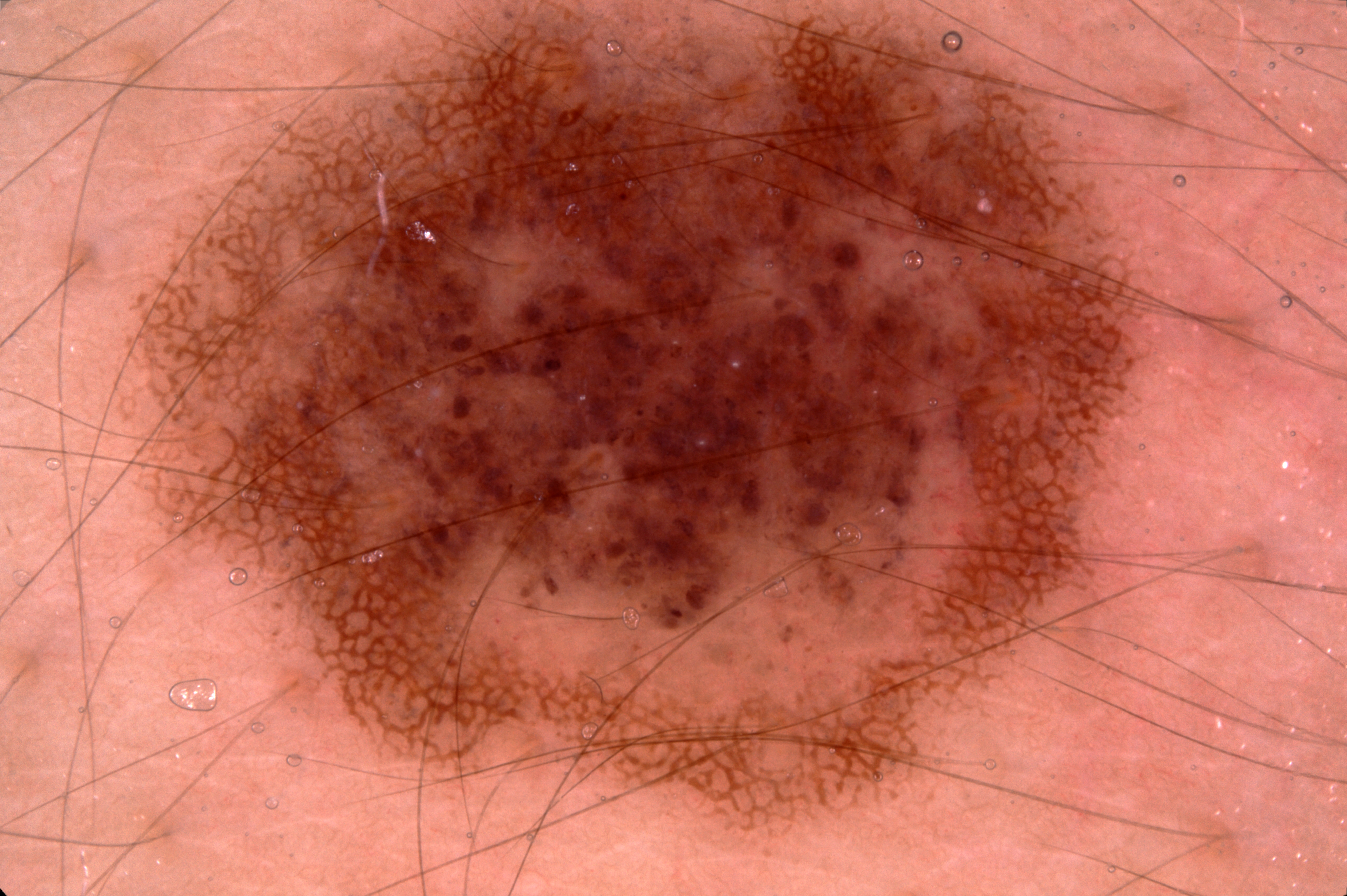image type = dermoscopy of a skin lesion | features = pigment network; absent: negative network, streaks, and milia-like cysts | lesion bbox = (127, 0, 1262, 832) | impression = a melanocytic nevus.